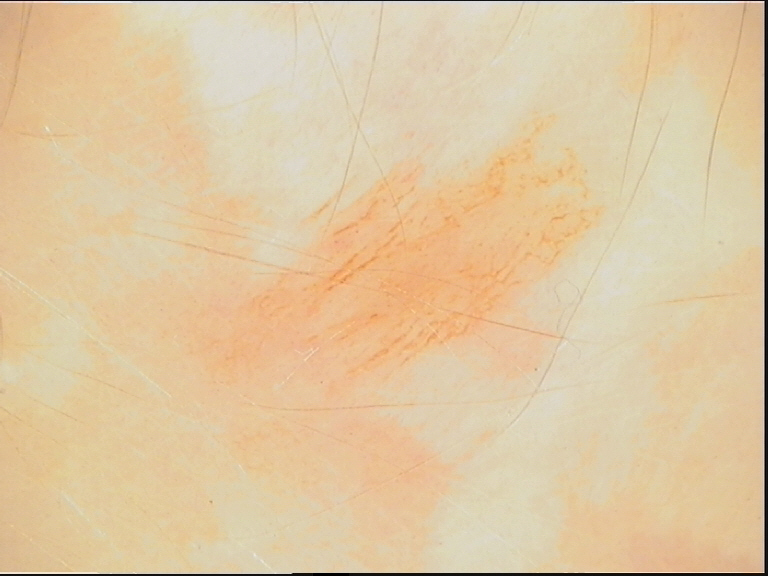A dermoscopy image of a single skin lesion.
Diagnosed as a benign lesion — an acral dysplastic junctional nevus.